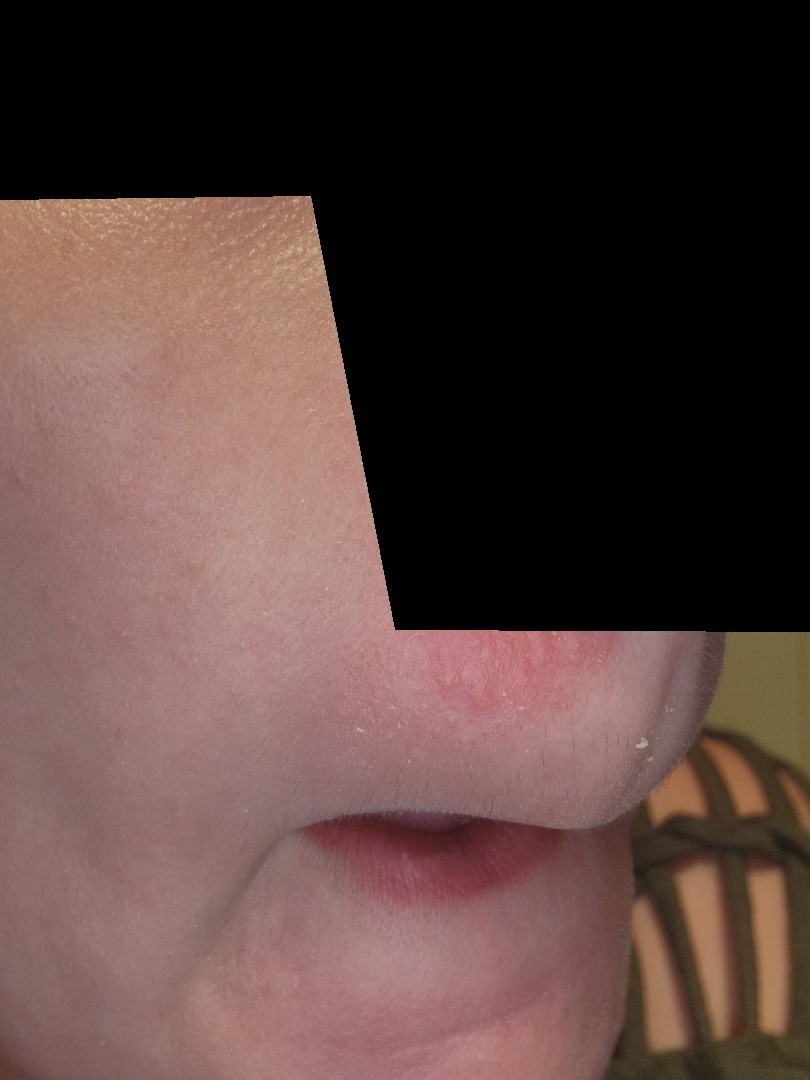differential diagnosis: the leading consideration is Perioral Dermatitis; less probable is Herpes Simplex; less likely is Seborrheic Dermatitis.